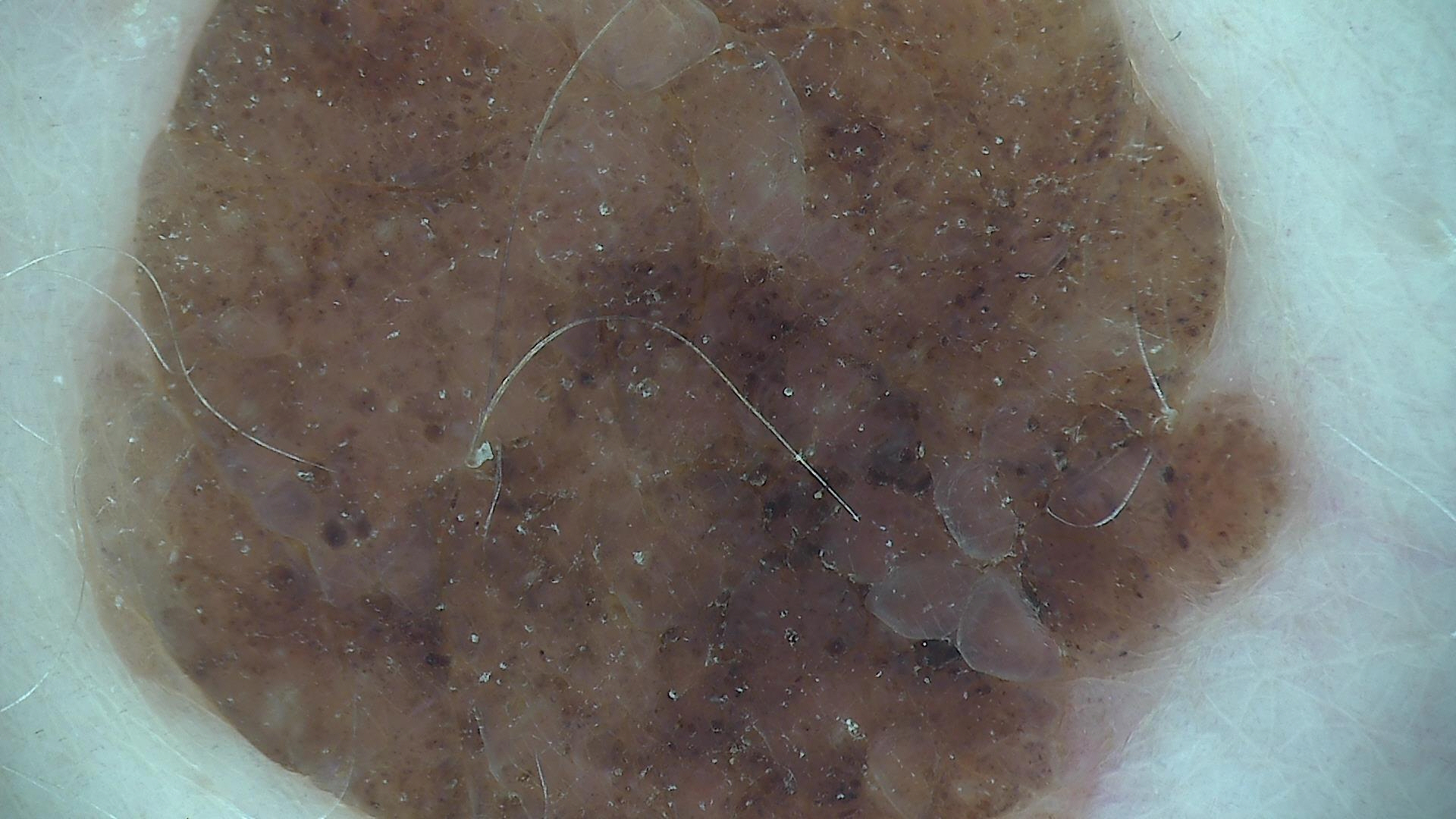<case>
<image>dermoscopy</image>
<diagnosis>
<name>compound nevus</name>
<code>cb</code>
<malignancy>benign</malignancy>
<super_class>melanocytic</super_class>
<confirmation>expert consensus</confirmation>
</diagnosis>
</case>